A skin lesion imaged with a dermatoscope: 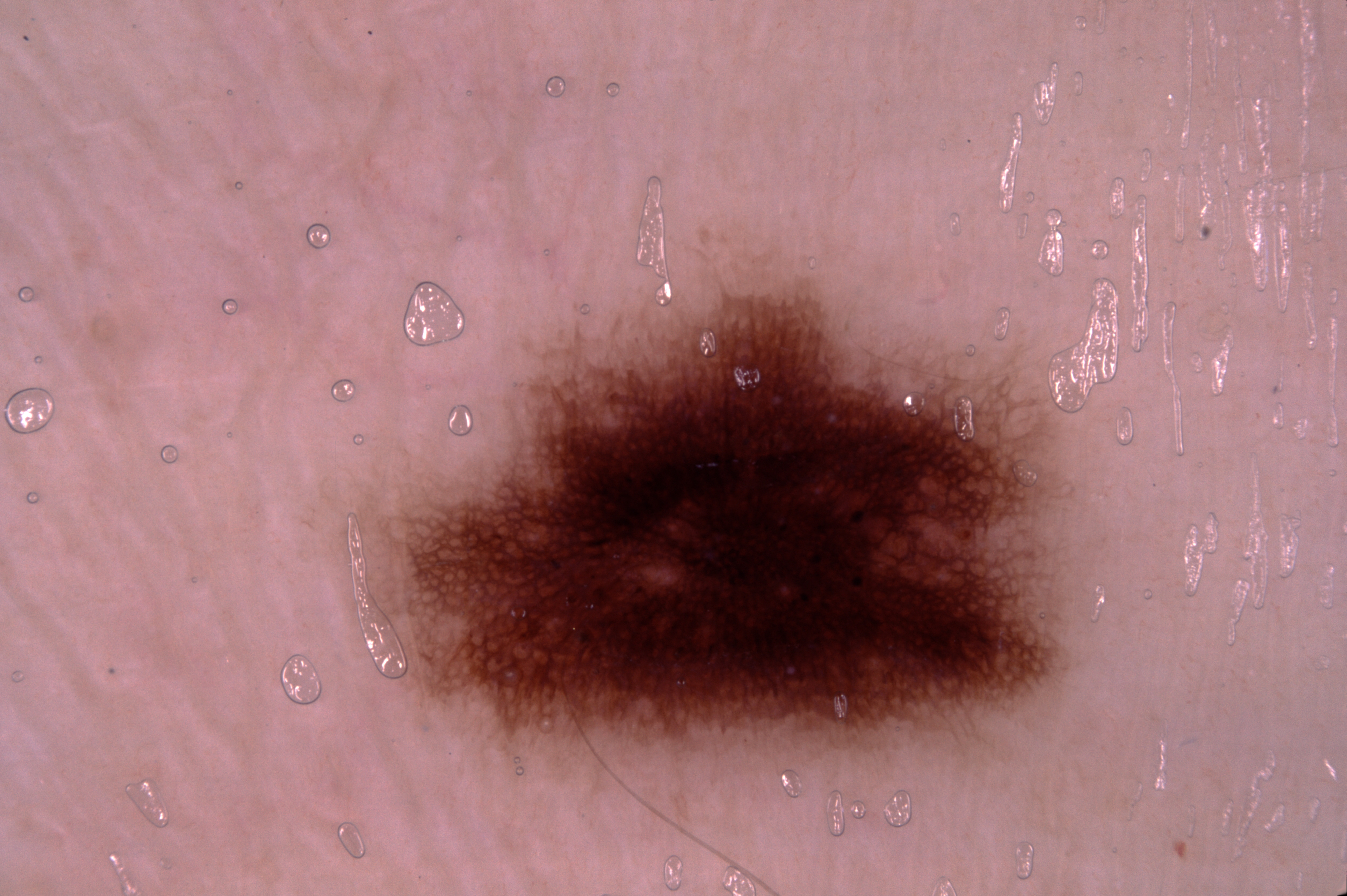As (left, top, right, bottom), lesion location: 369 278 1073 771. Consistent with a melanocytic nevus, a benign skin lesion.